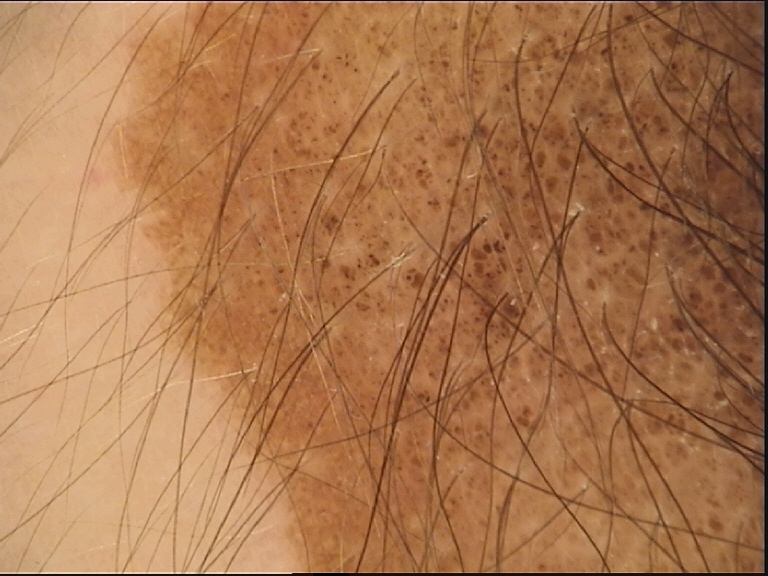Case: A dermoscopic close-up of a skin lesion. The morphology is that of a banal lesion. Conclusion: Consistent with a congenital compound nevus.